A dermoscopic close-up of a skin lesion. The patient is a female about 15 years old:
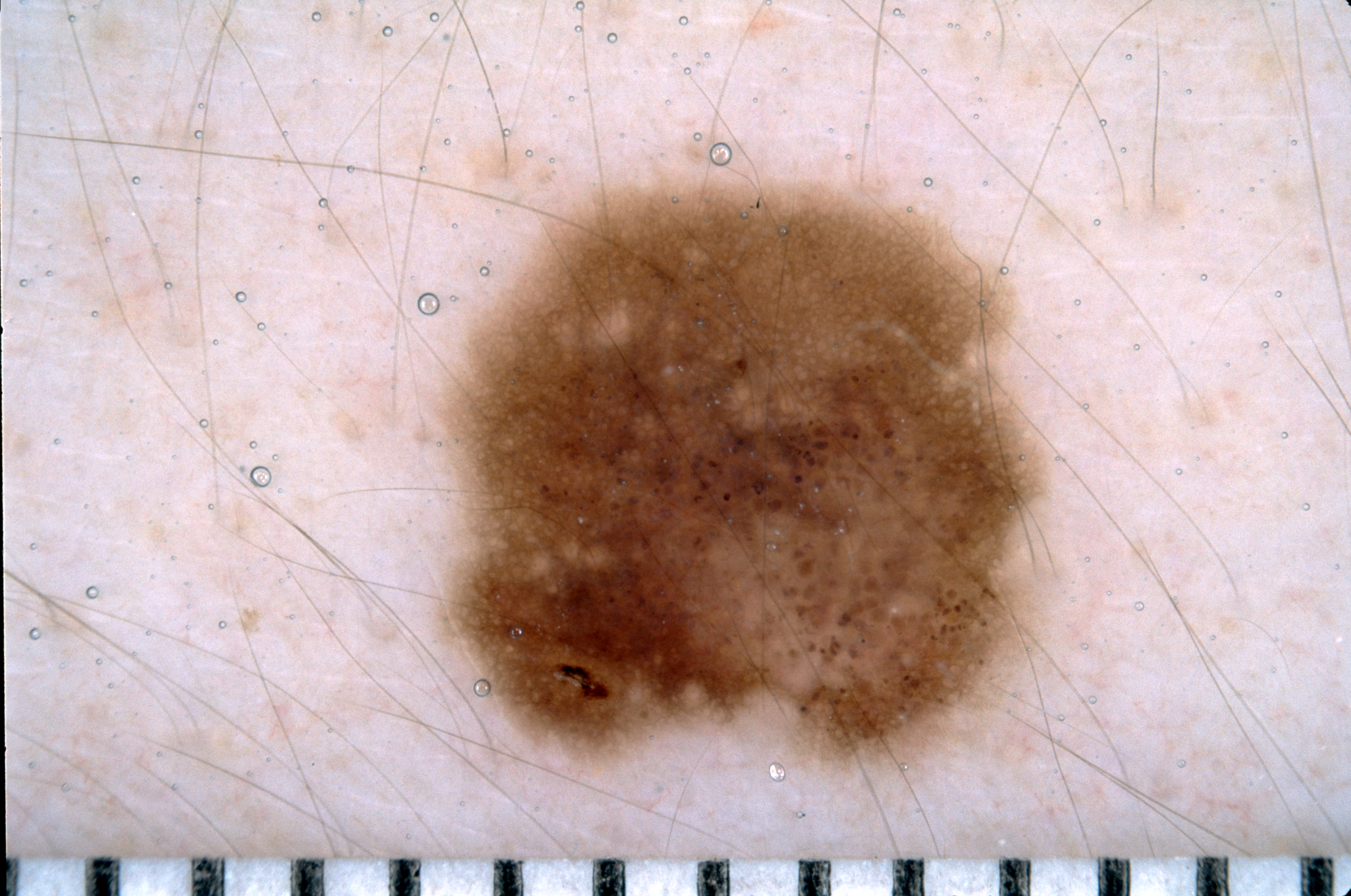The dermoscopic pattern shows pigment network and milia-like cysts. As (left, top, right, bottom), the lesion is located at box(441, 181, 1044, 777). Clinically diagnosed as a melanocytic nevus, a benign skin lesion.